A dermoscopy image of a single skin lesion.
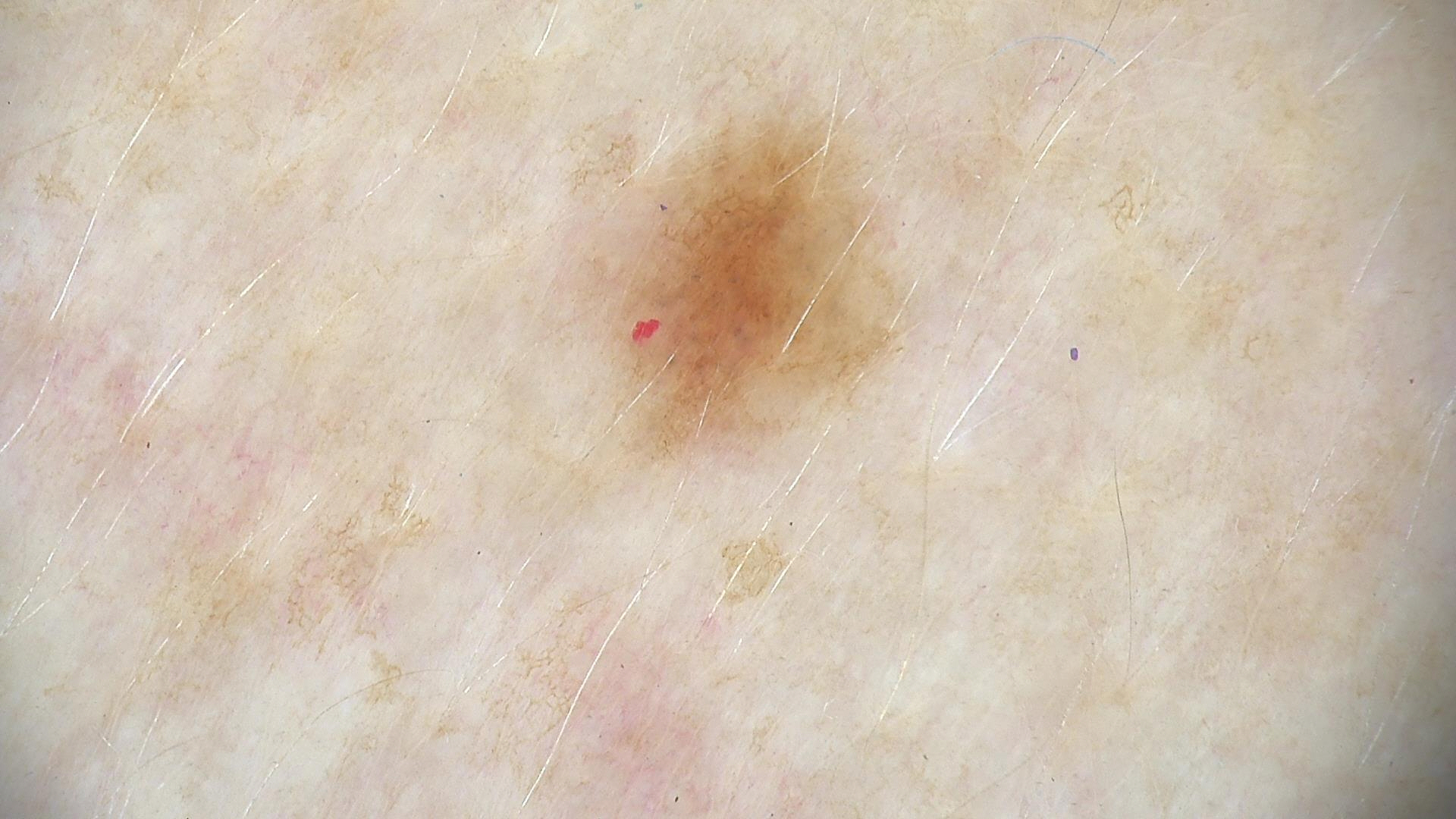{
  "diagnosis": {
    "name": "dysplastic junctional nevus",
    "code": "jd",
    "malignancy": "benign",
    "super_class": "melanocytic",
    "confirmation": "expert consensus"
  }
}